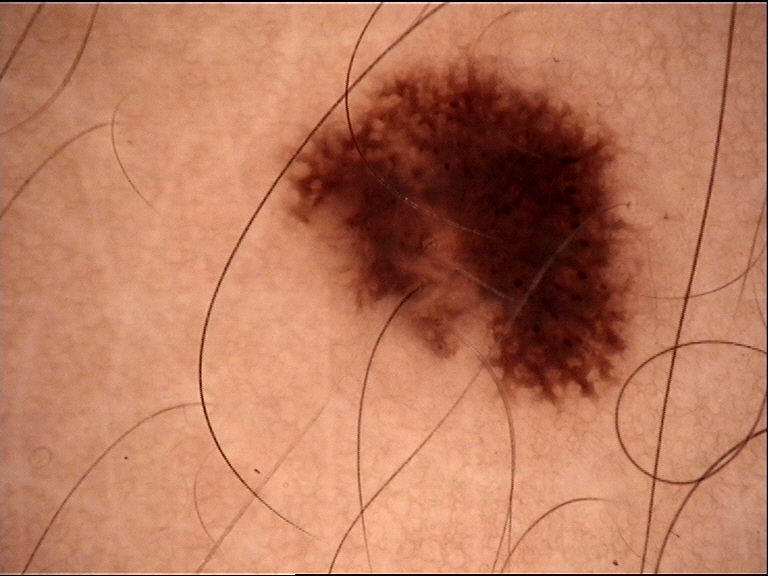Summary:
A dermatoscopic image of a skin lesion.
Conclusion:
Consistent with a dysplastic junctional nevus.